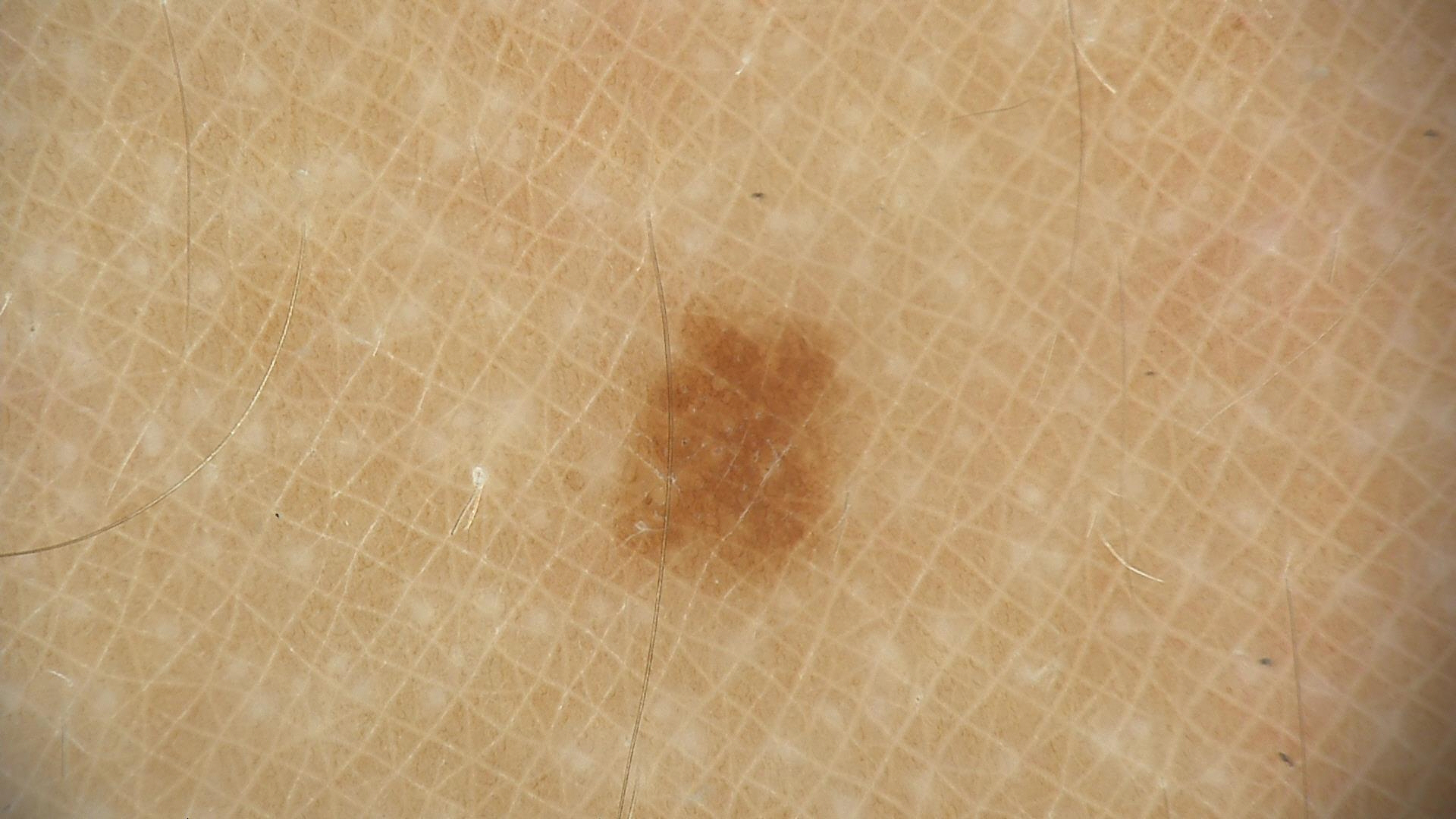diagnostic label — dysplastic junctional nevus (expert consensus).